Reported duration is less than one week; located on the front of the torso, arm and leg; the patient is 30–39, female; the lesion is associated with bothersome appearance, itching and enlargement; a close-up photograph; the patient considered this a rash; the lesion is described as raised or bumpy.
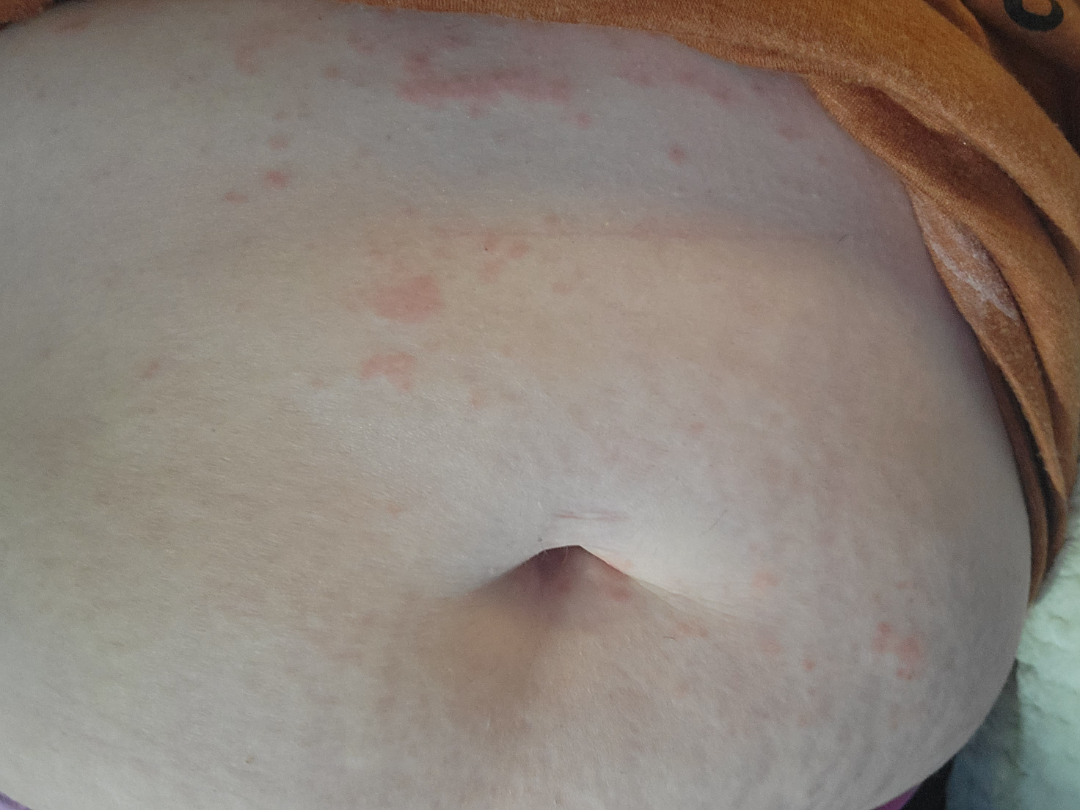Review:
The dermatologist could not determine a likely condition from the photograph alone.